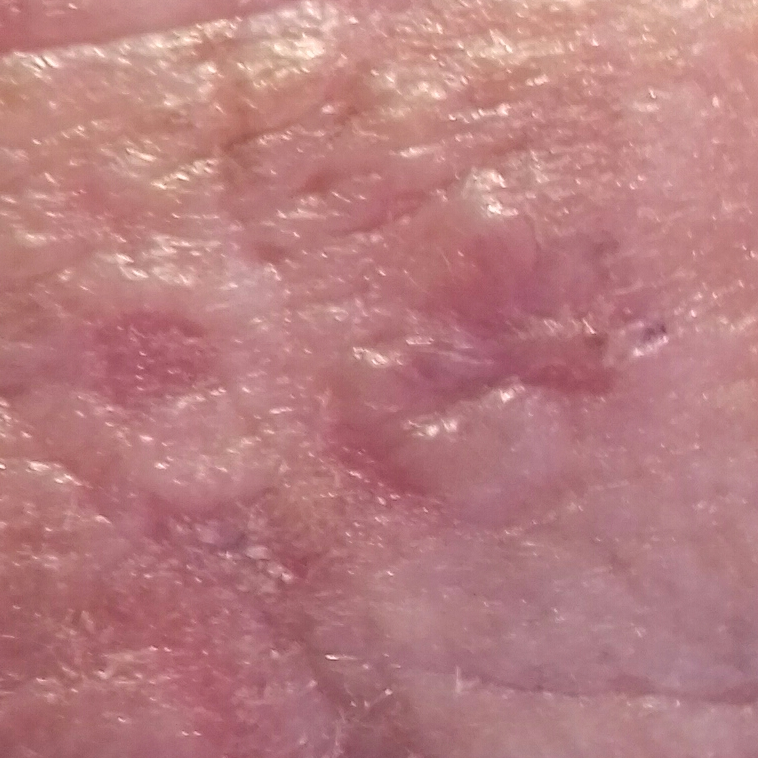image type — clinical photo; skin phototype — II; region — the face; patient-reported symptoms — elevation, itching; diagnosis — basal cell carcinoma (biopsy-proven).